A dermoscopic image of a skin lesion.
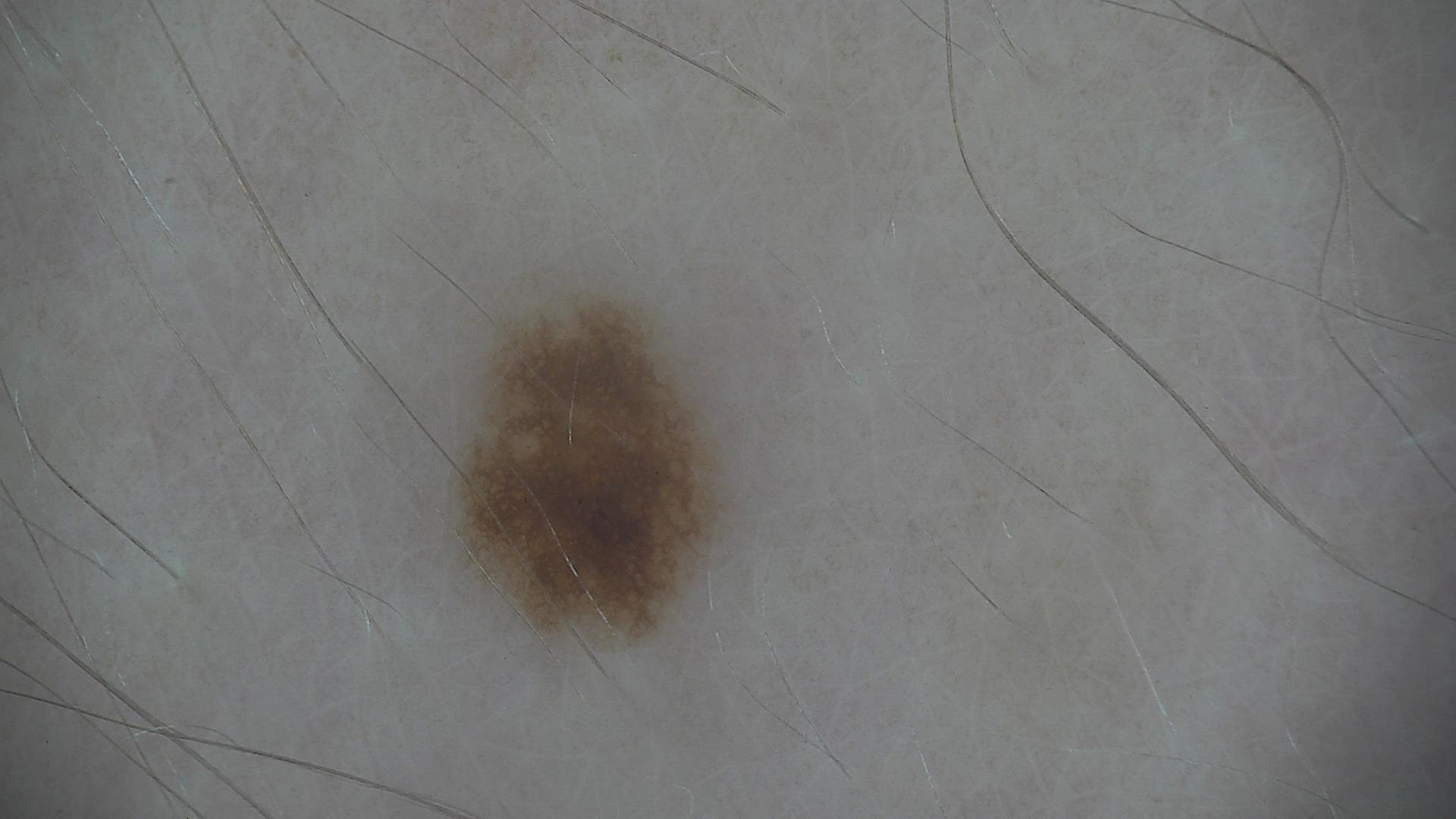<dermoscopy>
  <diagnosis>
    <name>dysplastic junctional nevus</name>
    <code>jd</code>
    <malignancy>benign</malignancy>
    <super_class>melanocytic</super_class>
    <confirmation>expert consensus</confirmation>
  </diagnosis>
</dermoscopy>